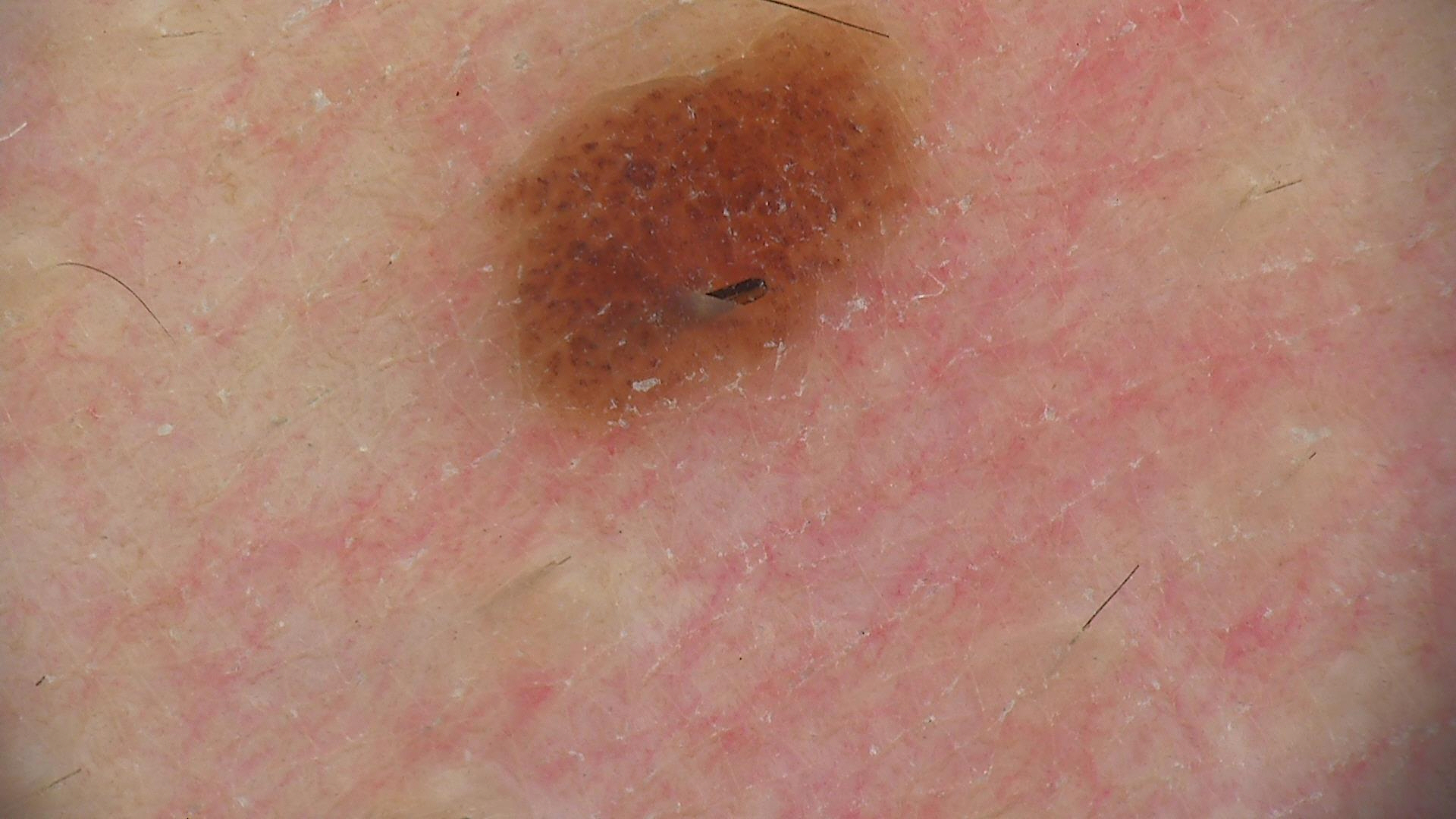image: dermatoscopy | subtype: banal | assessment: junctional nevus (expert consensus).